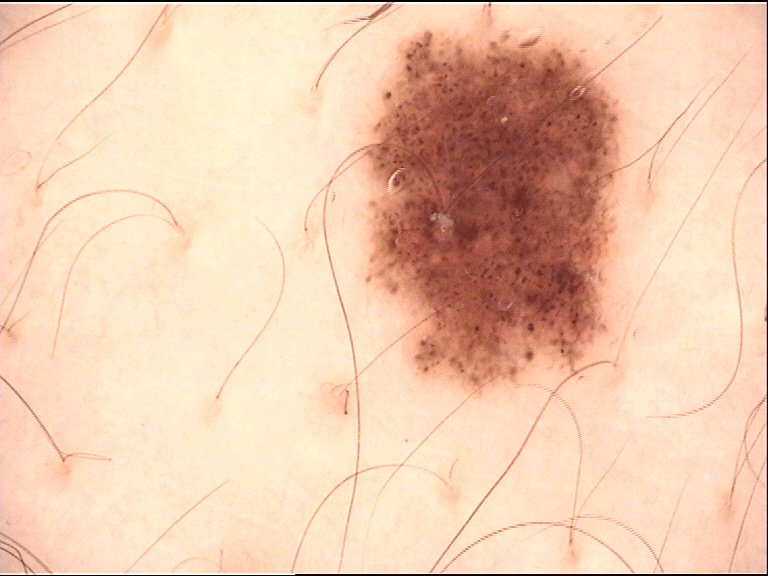label = dysplastic junctional nevus (expert consensus).